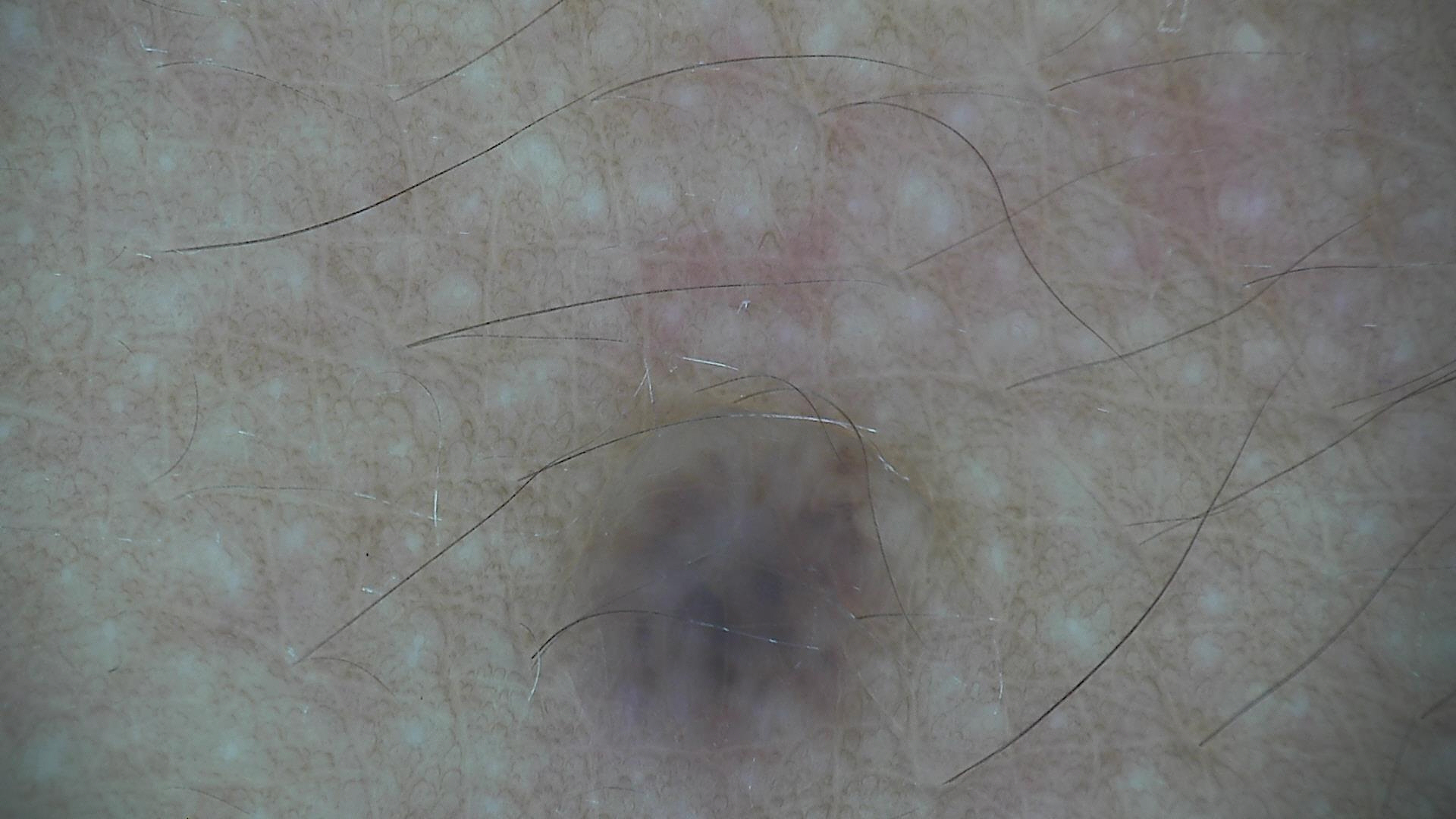| feature | finding |
|---|---|
| image type | dermatoscopy |
| class | dermal nevus (expert consensus) |